A skin lesion imaged with a dermatoscope. A female patient about 45 years old.
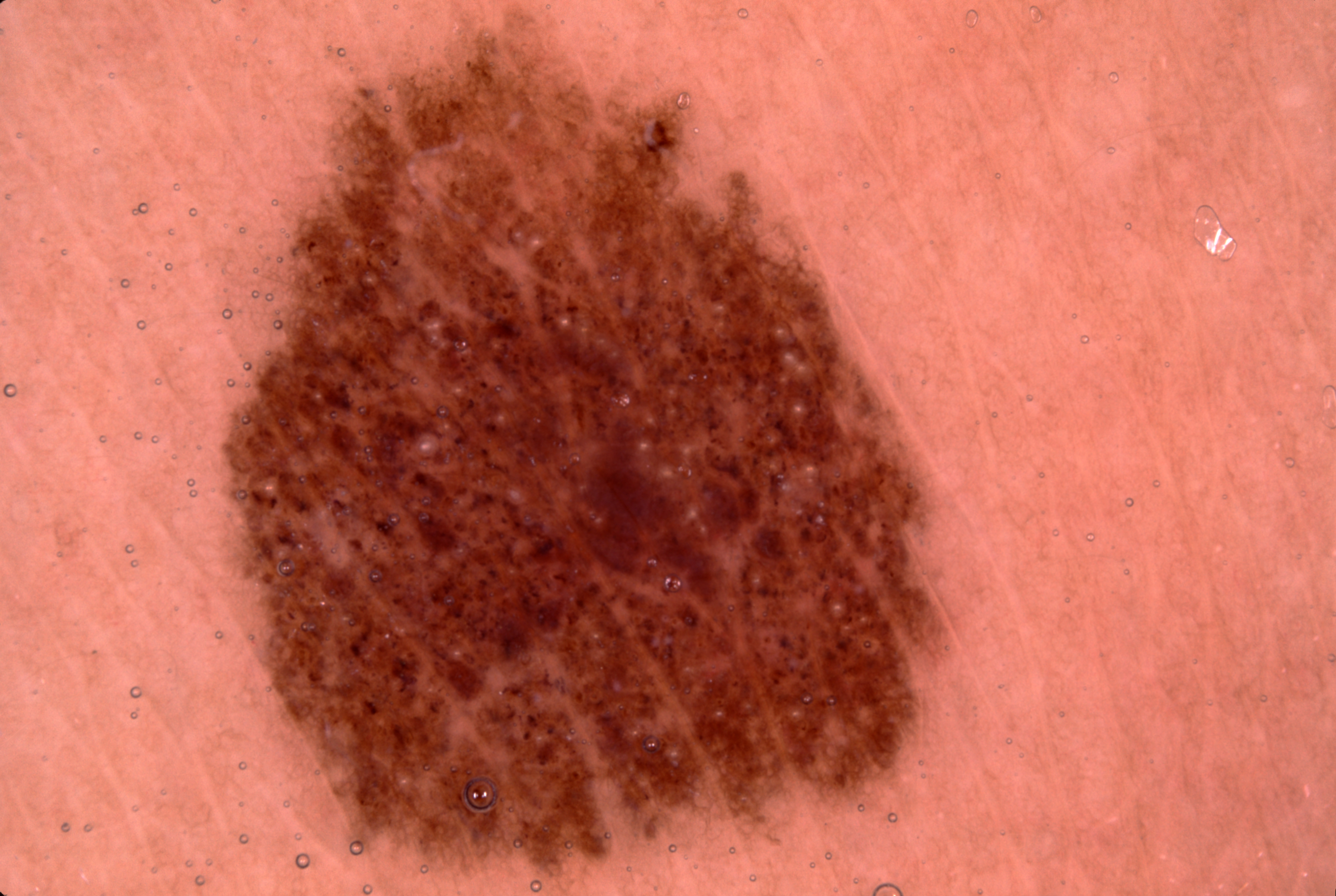Q: Where is the lesion in the image?
A: [219, 10, 957, 893]
Q: What dermoscopic features are present?
A: pigment network and milia-like cysts
Q: How much of the field does the lesion occupy?
A: ~37% of the field
Q: What is the diagnosis?
A: a melanocytic nevus, a benign lesion